Present for one to three months · located on the leg · the patient described the issue as hair loss · the photograph was taken at a distance · female patient, age 40–49 · the patient notes bothersome appearance · texture is reported as flat:
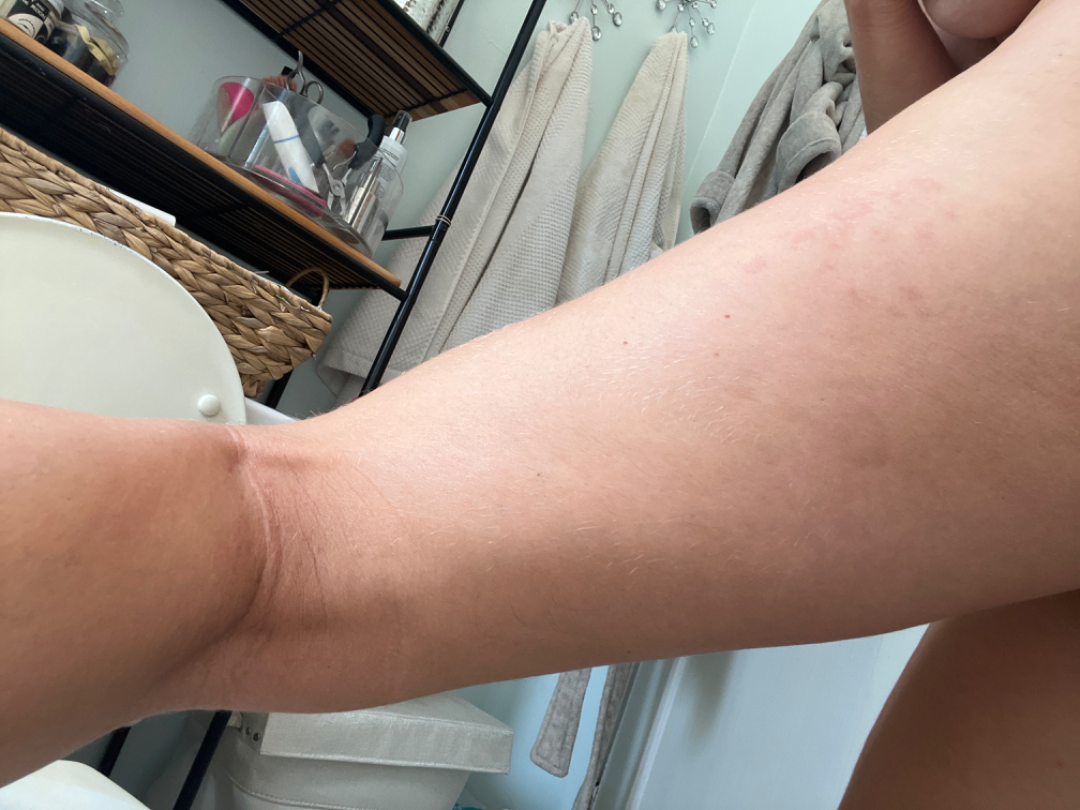Q: What is the dermatologist's impression?
A: the leading consideration is Hypersensitivity; also on the differential is Eczema